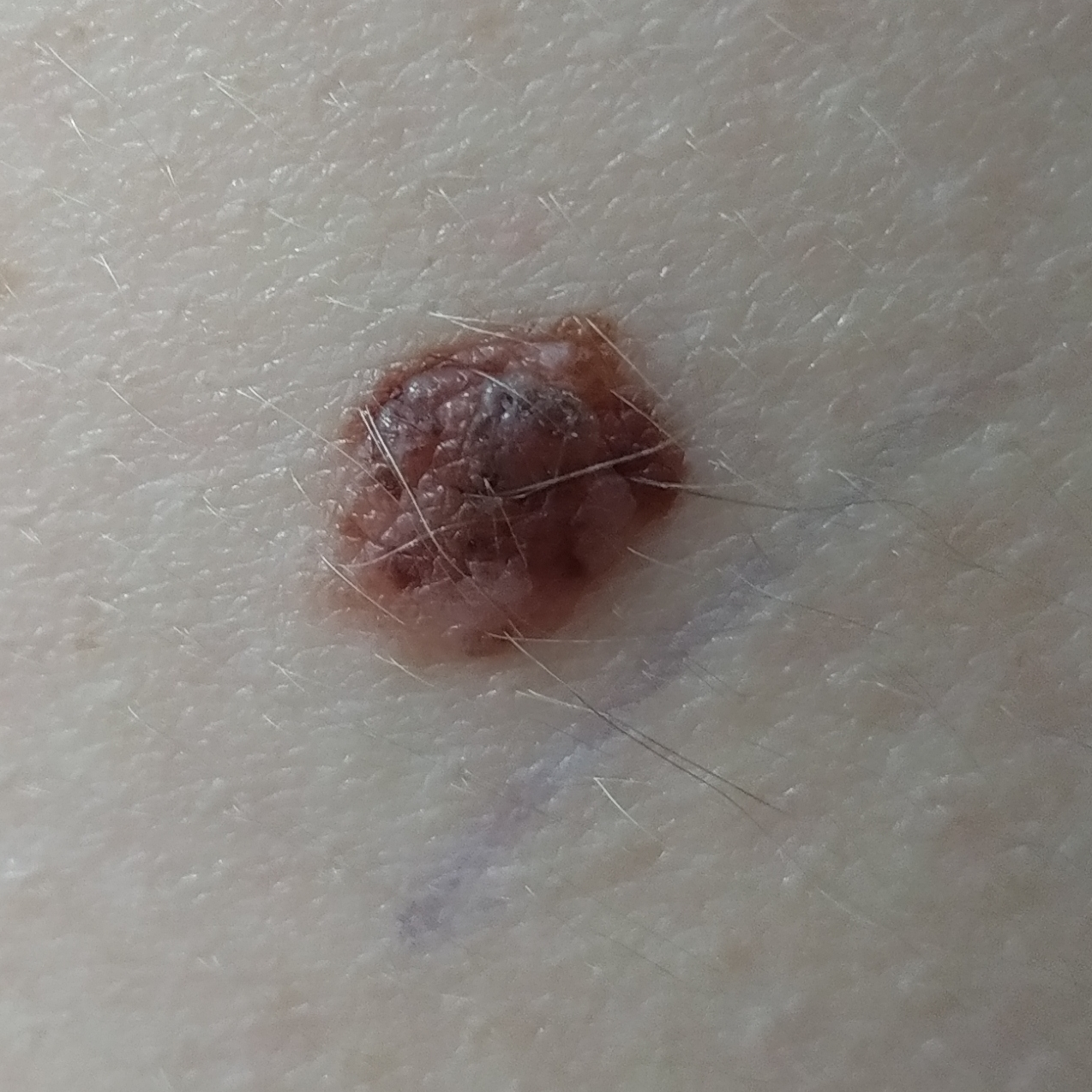A female subject age 30.
Recorded as Fitzpatrick III.
The chart records prior skin cancer (patient or family) and prior malignancy (patient or family).
A clinical photograph of a skin lesion.
Located on the back.
The lesion measures approximately 6 × 6 mm.
The patient reports that the lesion is elevated.
The biopsy diagnosis was a nevus.